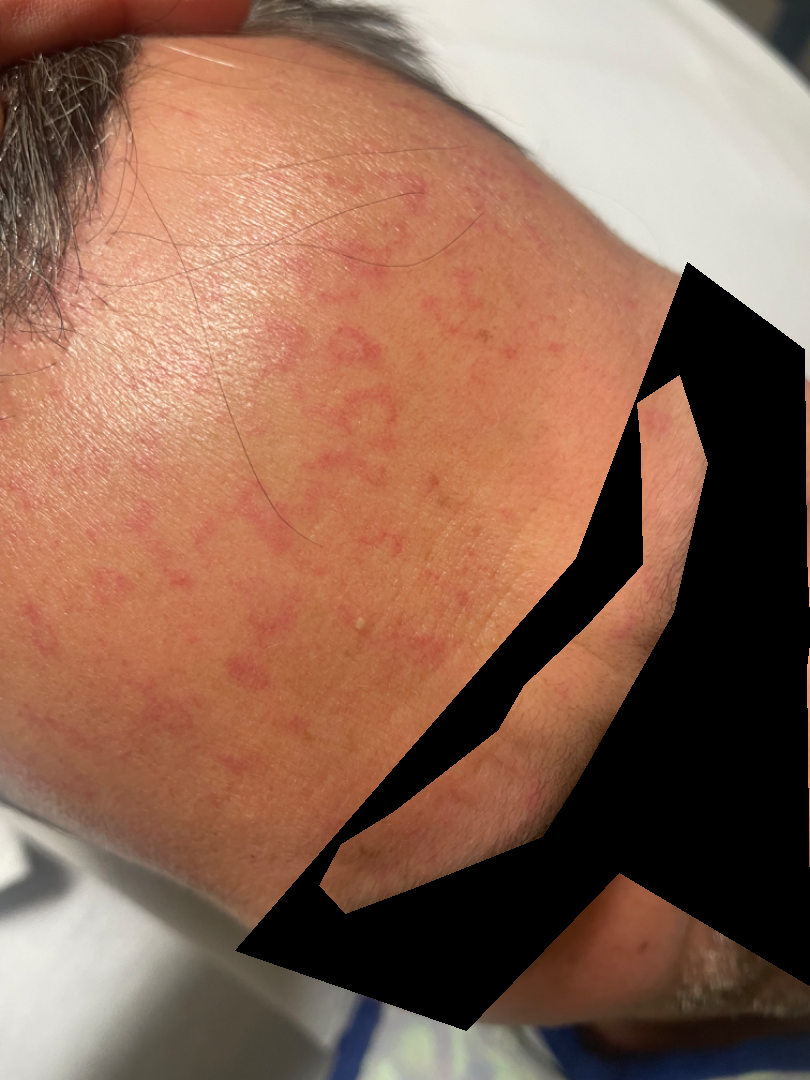Q: What was the assessment?
A: indeterminate from the photograph
Q: What is the affected area?
A: front of the torso, head or neck, leg, arm and back of the torso
Q: Age and sex?
A: male, age 40–49
Q: What is the lesion texture?
A: flat
Q: How was the photo taken?
A: close-up
Q: Duration?
A: three to twelve months
Q: Reported symptoms?
A: burning and itching